The photo was captured at an angle. The back of the hand is involved. The contributor is a female aged 40–49.
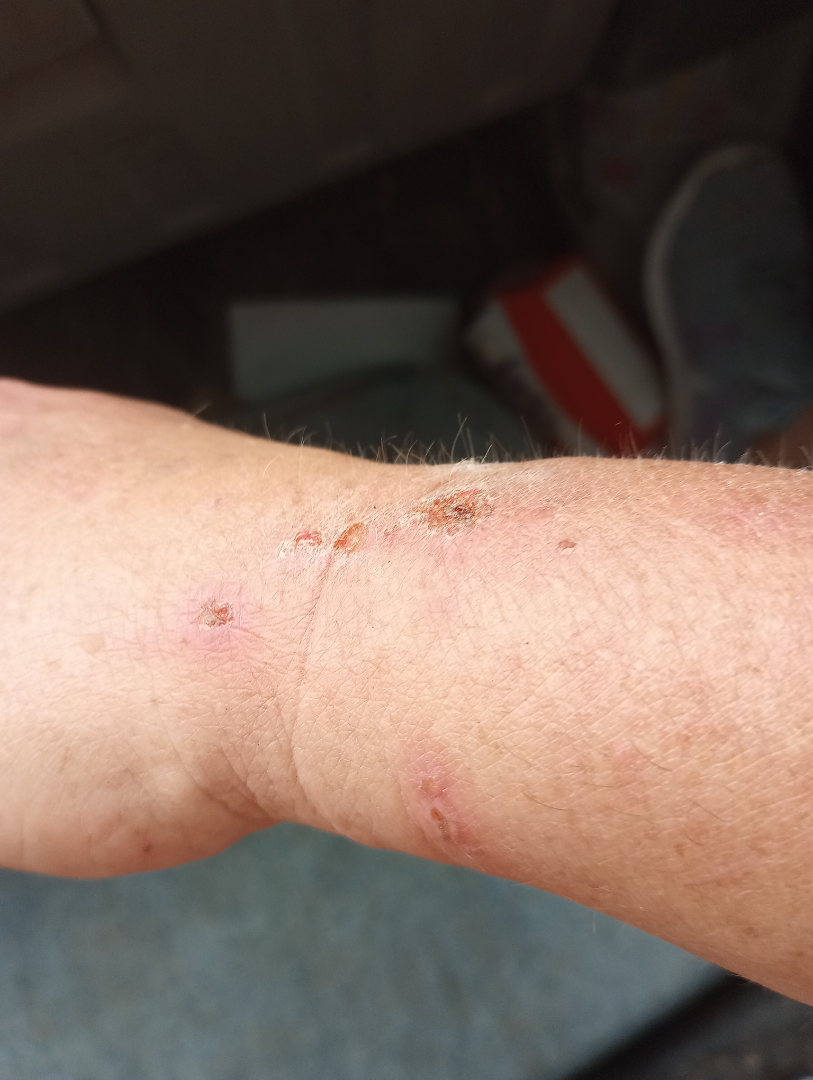Findings:
Diagnostic features were not clearly distinguishable in this photograph.